A dermoscopic photograph of a skin lesion.
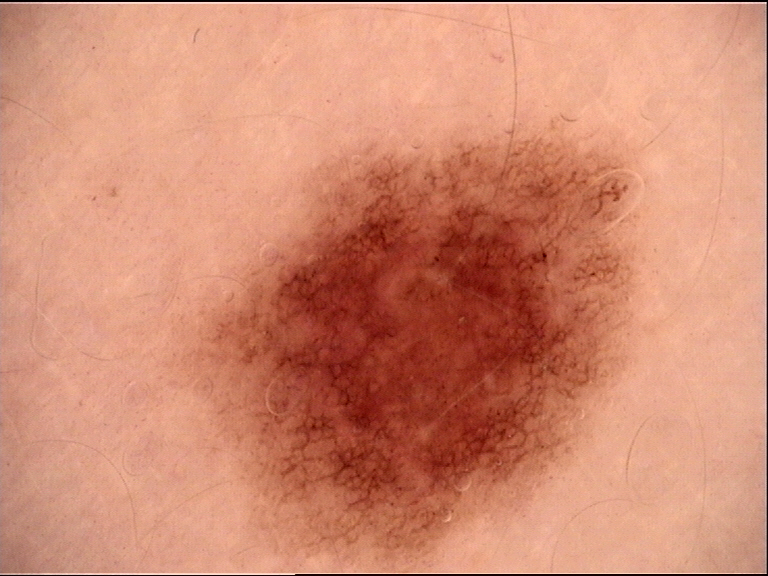diagnosis: dysplastic compound nevus (expert consensus).